Reported duration is less than one week; associated systemic symptoms include fatigue and joint pain; close-up view; the lesion involves the back of the hand; reported lesion symptoms include pain, burning, bothersome appearance and itching; the patient is a male aged 50–59; the patient notes the lesion is raised or bumpy; the patient considered this a rash: 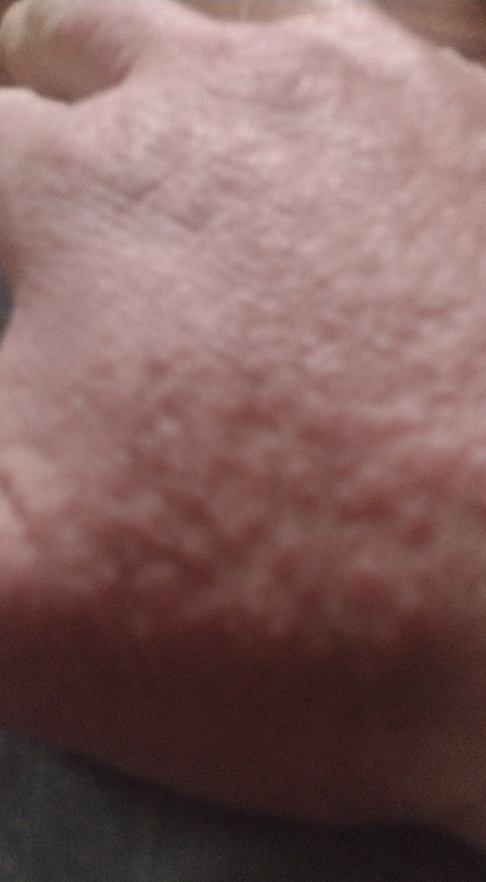Q: Could the case be diagnosed?
A: could not be assessed